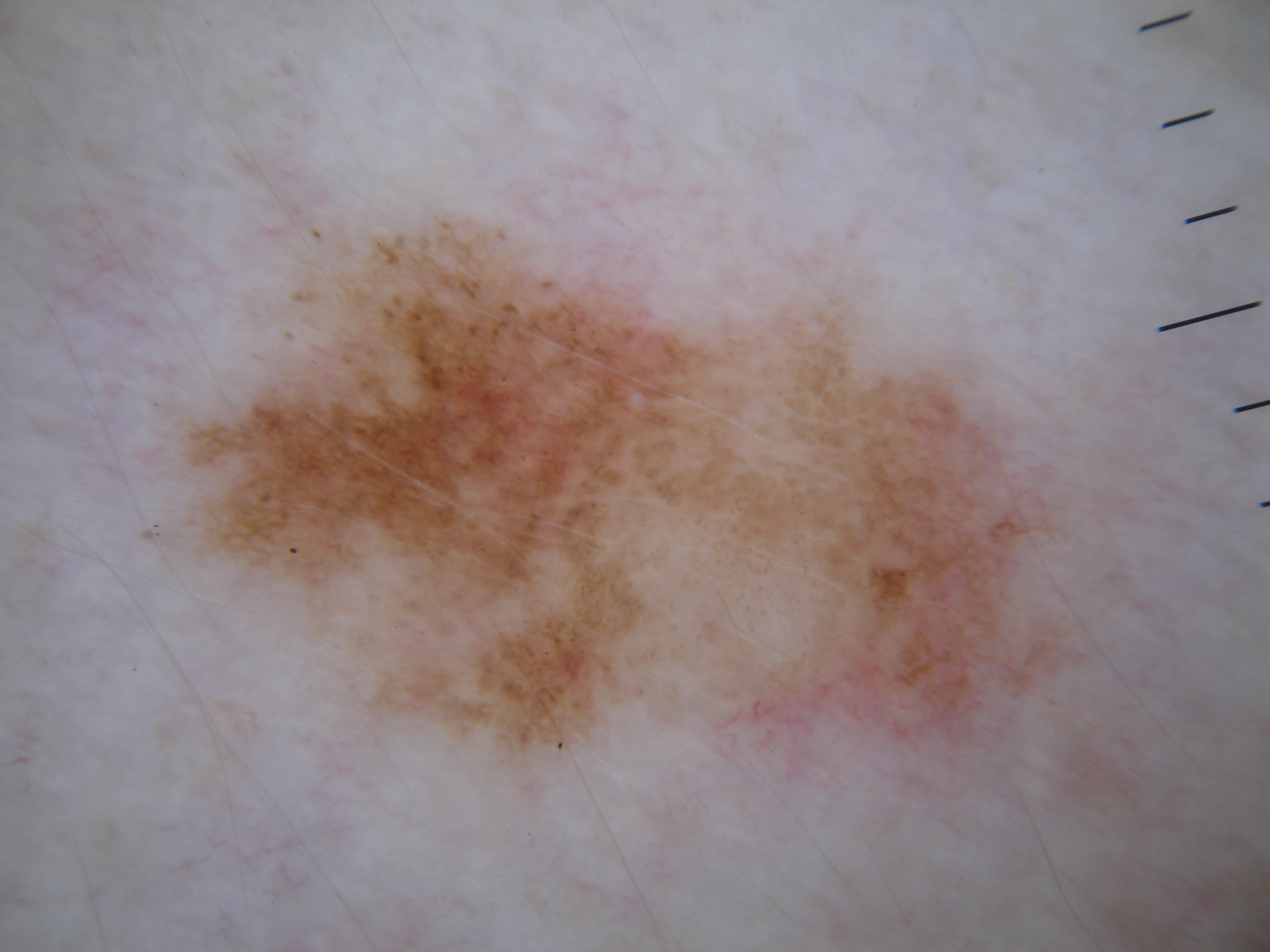This is a dermoscopic photograph of a skin lesion. Dermoscopic examination shows negative network, globules, and pigment network; no milia-like cysts or streaks. The lesion occupies roughly 32% of the field. The lesion is bounded by <box>142, 208, 1094, 813</box>. Clinically diagnosed as a melanocytic nevus.